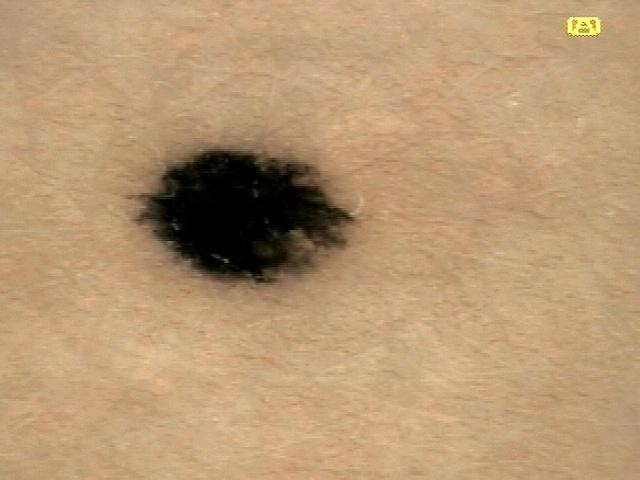Conclusion: Histopathological examination showed a melanoma.